FST II; lay reviewers estimated 2 on the Monk skin tone scale · an image taken at a distance — 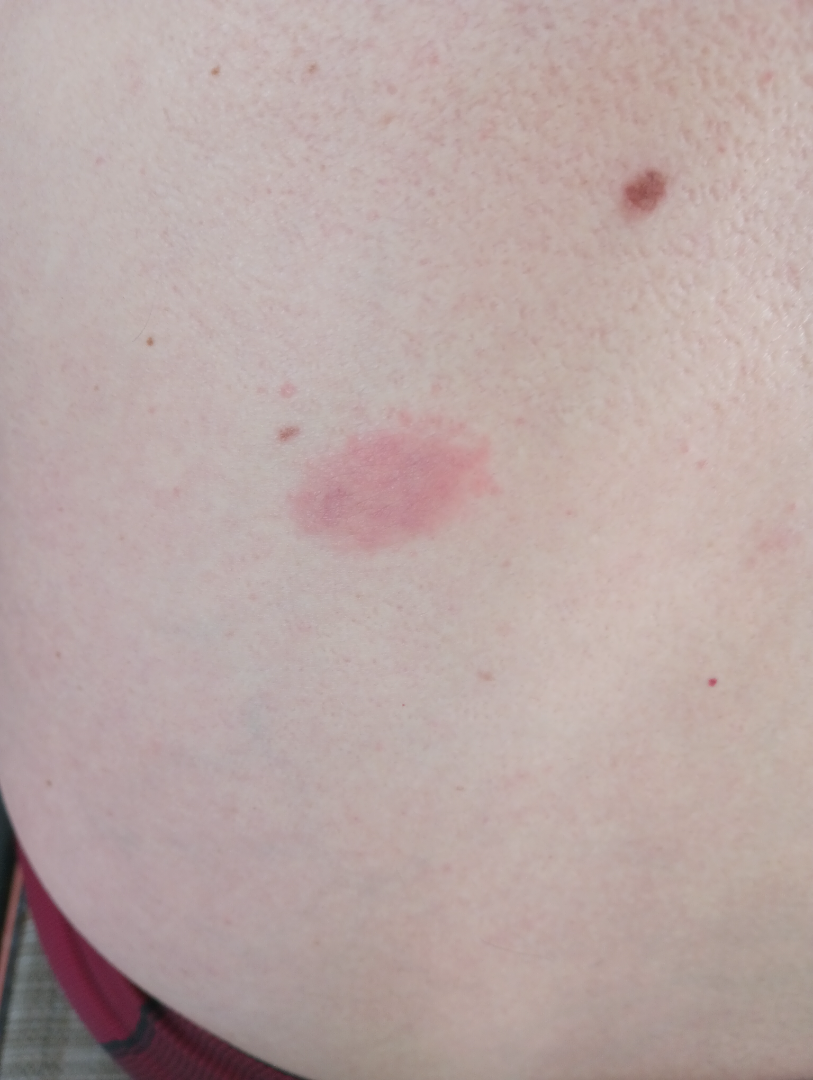Diagnostic features were not clearly distinguishable in this photograph.